The photo was captured at an angle — 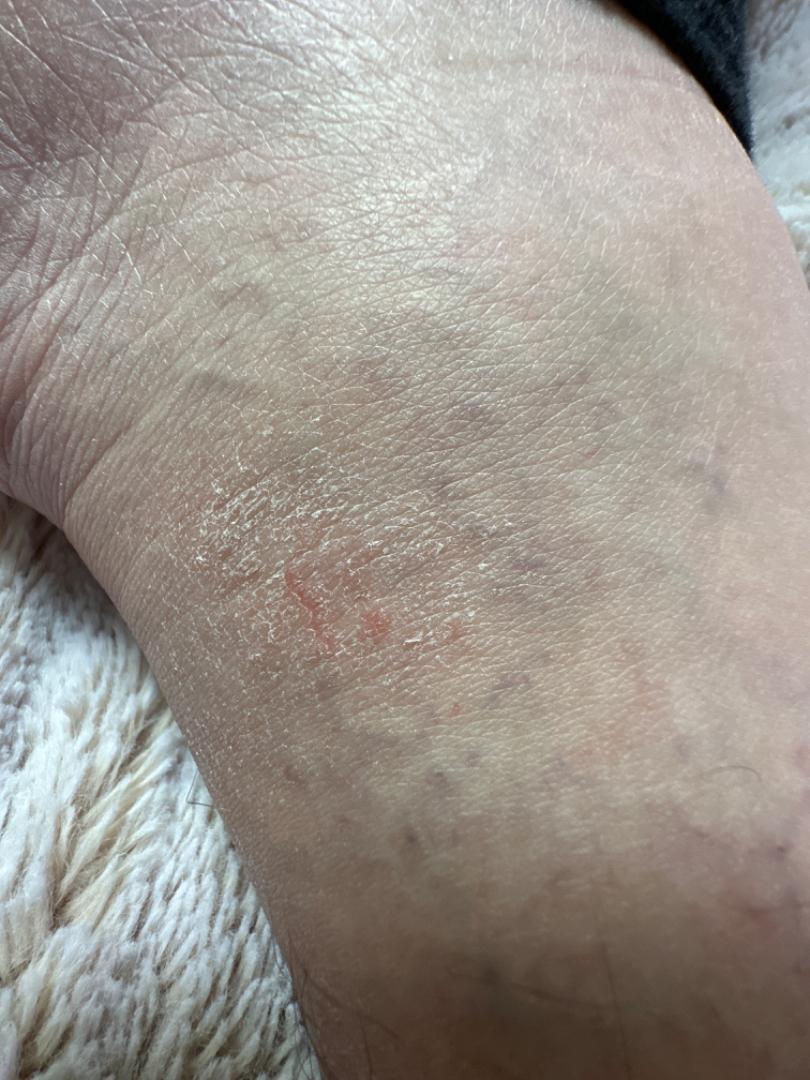{"skin_tone": {"fitzpatrick": "V"}, "differential": {"tied_lead": ["Eczema", "Stasis Dermatitis"]}}